The back of the hand is involved. This image was taken at an angle. The subject is 30–39, female.
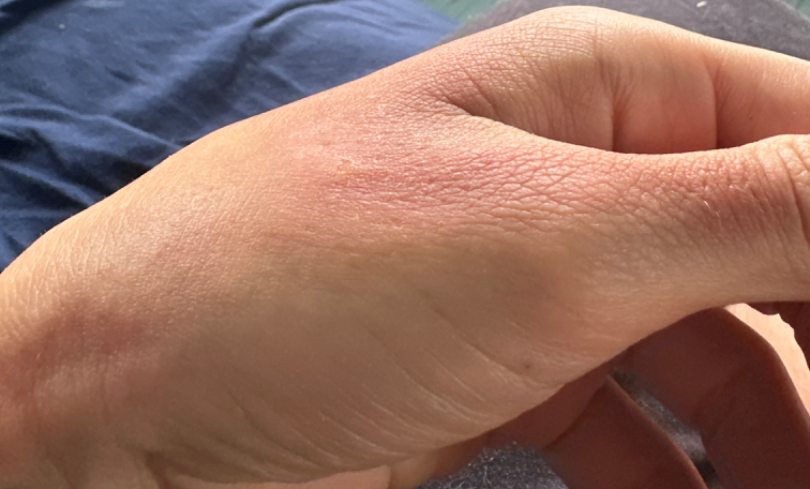<case>
<duration>one to four weeks</duration>
<symptoms>burning, itching, bothersome appearance, pain, darkening</symptoms>
<patient_category>a rash</patient_category>
<differential>
  <leading>Irritant Contact Dermatitis</leading>
  <considered>Allergic Contact Dermatitis</considered>
</differential>
</case>